The patient notes bothersome appearance, enlargement and itching · the lesion is described as raised or bumpy · the photo was captured at an angle · present for one to four weeks · the affected area is the palm — 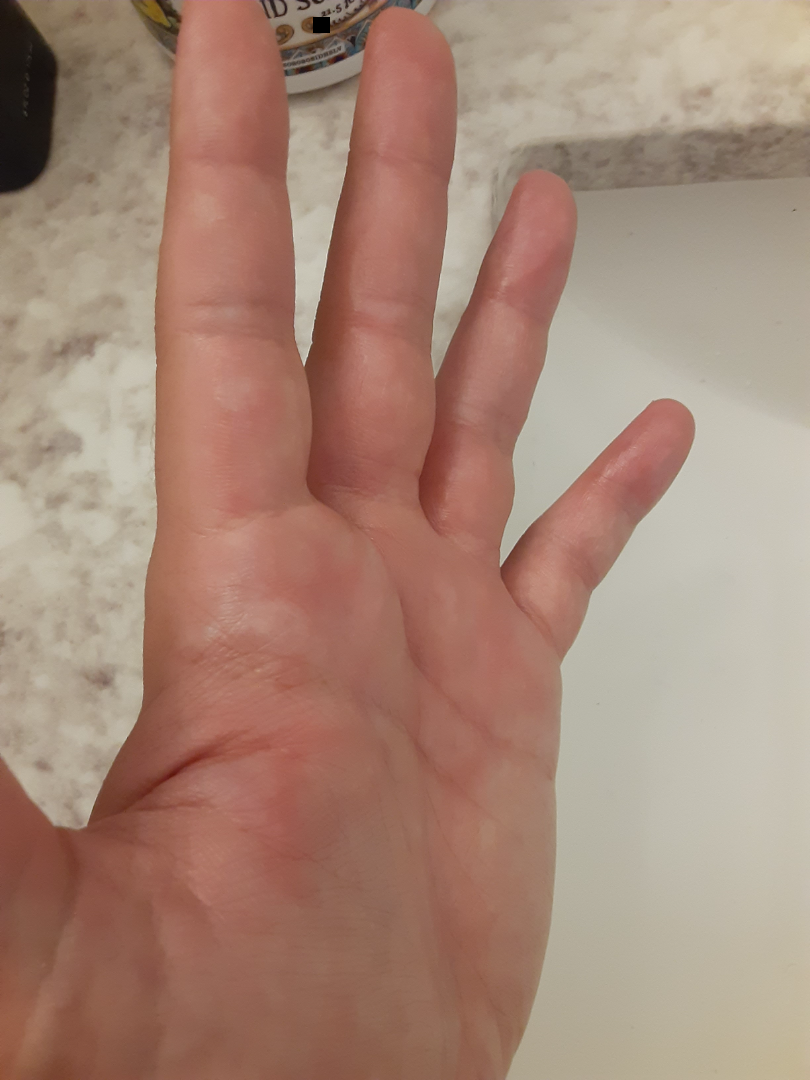impression = Viral Exanthem, Chilblain and Erythema multiforme were each considered, in no particular order